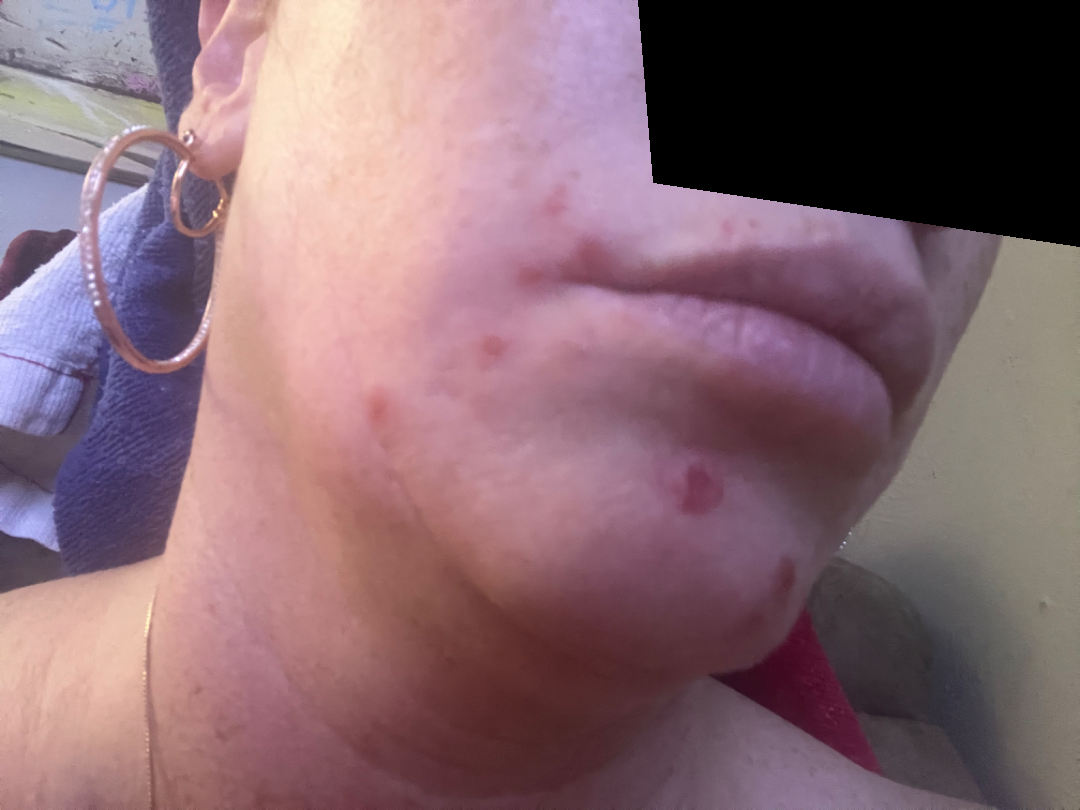Q: What is the dermatologist's impression?
A: the reviewer's impression was Acne